A skin lesion imaged with a dermatoscope:
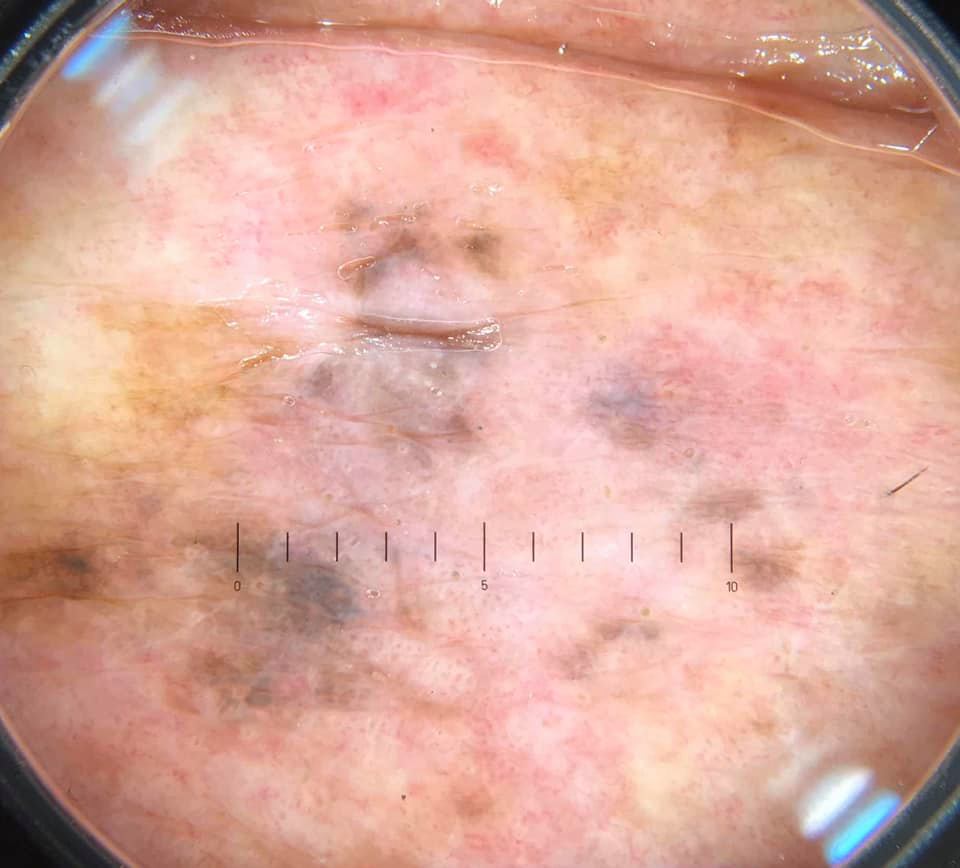Diagnosis: Confirmed on histopathology as a lentigo maligna.